Located on the back of the torso, back of the hand, front of the torso, arm and leg · the photograph was taken at a distance · female contributor, age 18–29 — 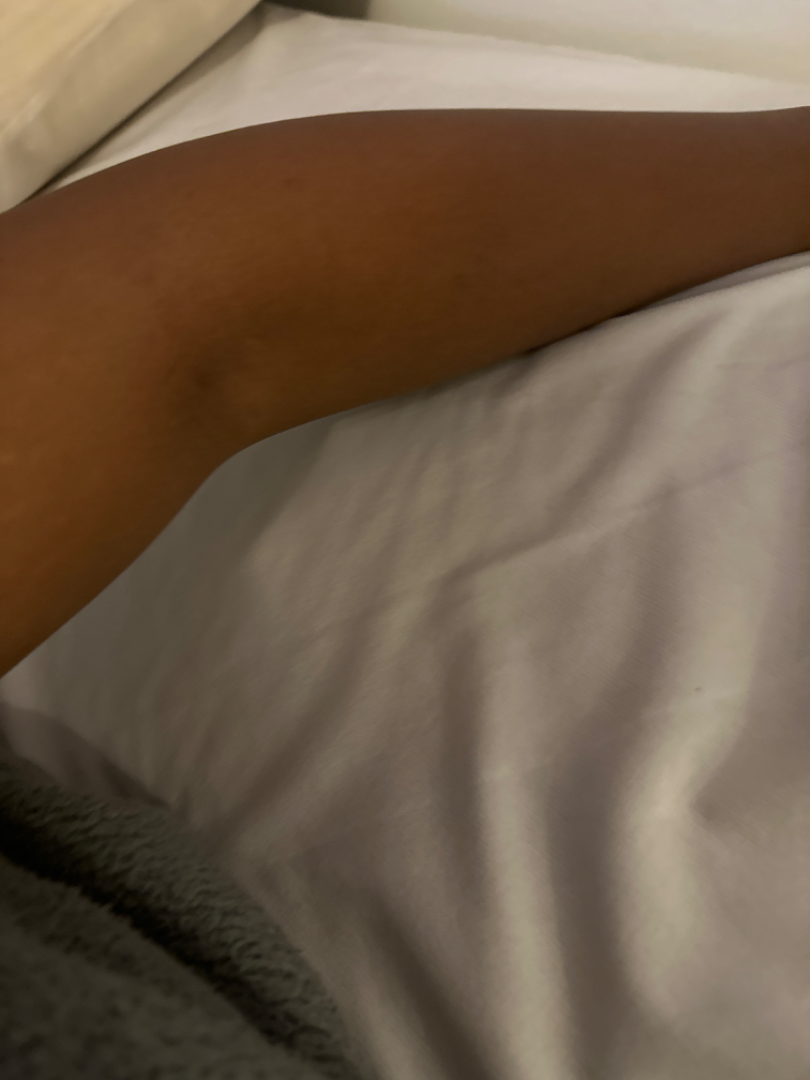assessment=indeterminate from the photograph.